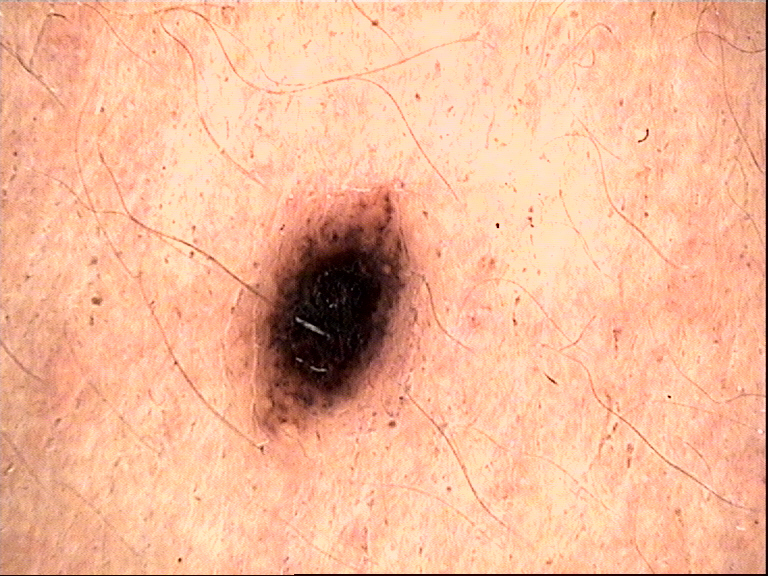image: dermatoscopy
label: dysplastic compound nevus (expert consensus)